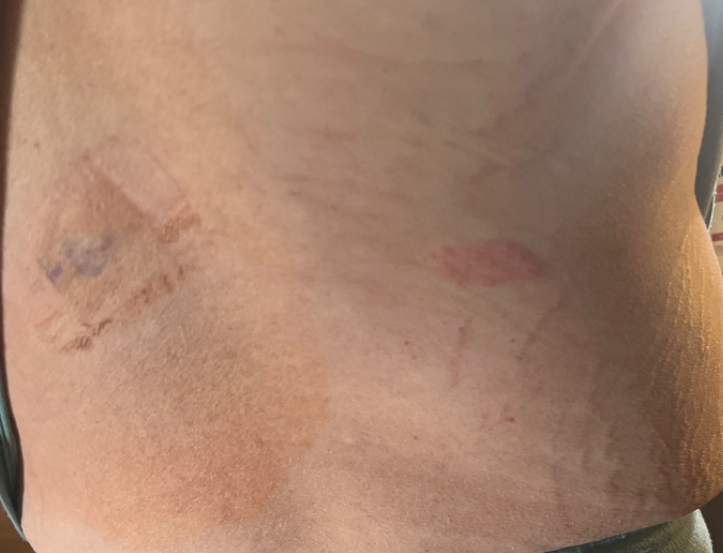Patient information:
The photo was captured at a distance.
Review:
On teledermatology review, Eczema (leading).